Close-up view; the leg is involved; lay graders estimated MST 3 or 4 (two reviewer pools); the patient is 40–49, female; present for about one day; symptoms reported: itching and bothersome appearance.
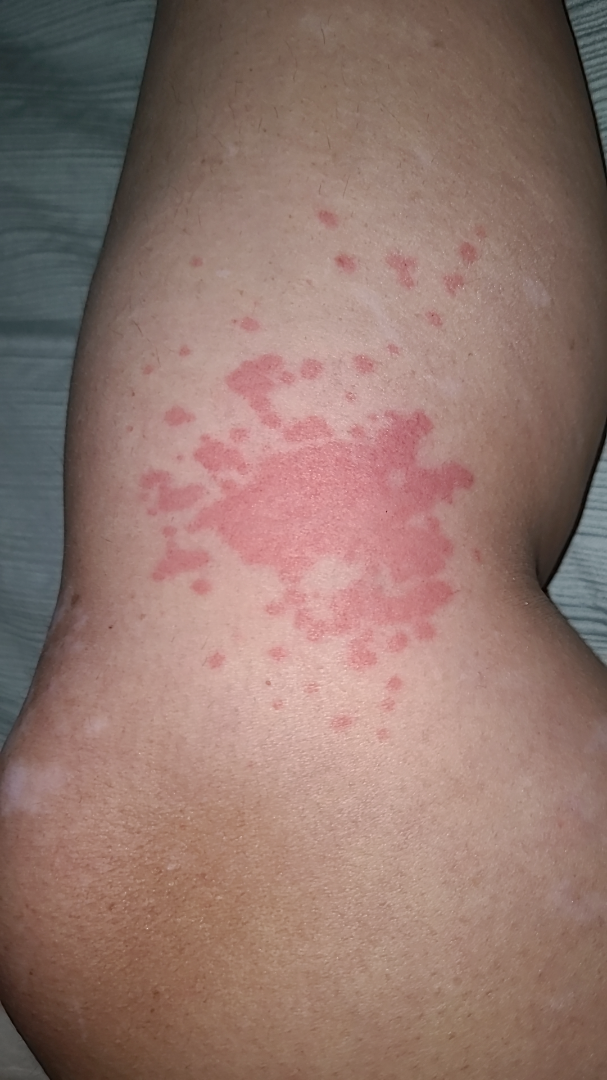On photographic review by a dermatologist, the differential is split between Urticaria, Insect Bite and Allergic Contact Dermatitis.